The photograph was taken at an angle:
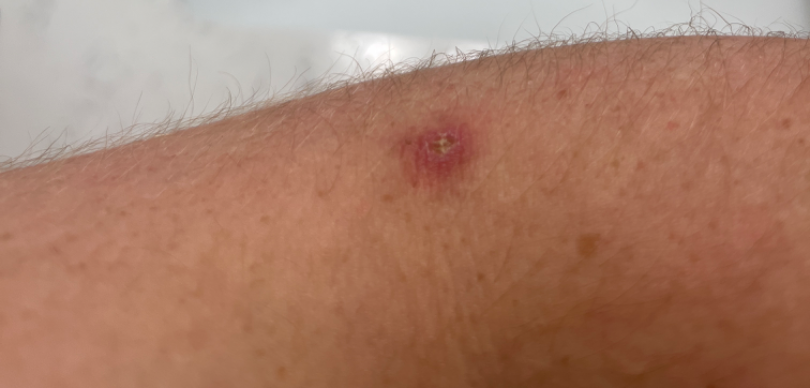On remote review of the image, the differential, in no particular order, includes Ecthyma and Abscess.